The patient was assessed as FST I. A female subject aged approximately 35. A dermoscopic image of a skin lesion.
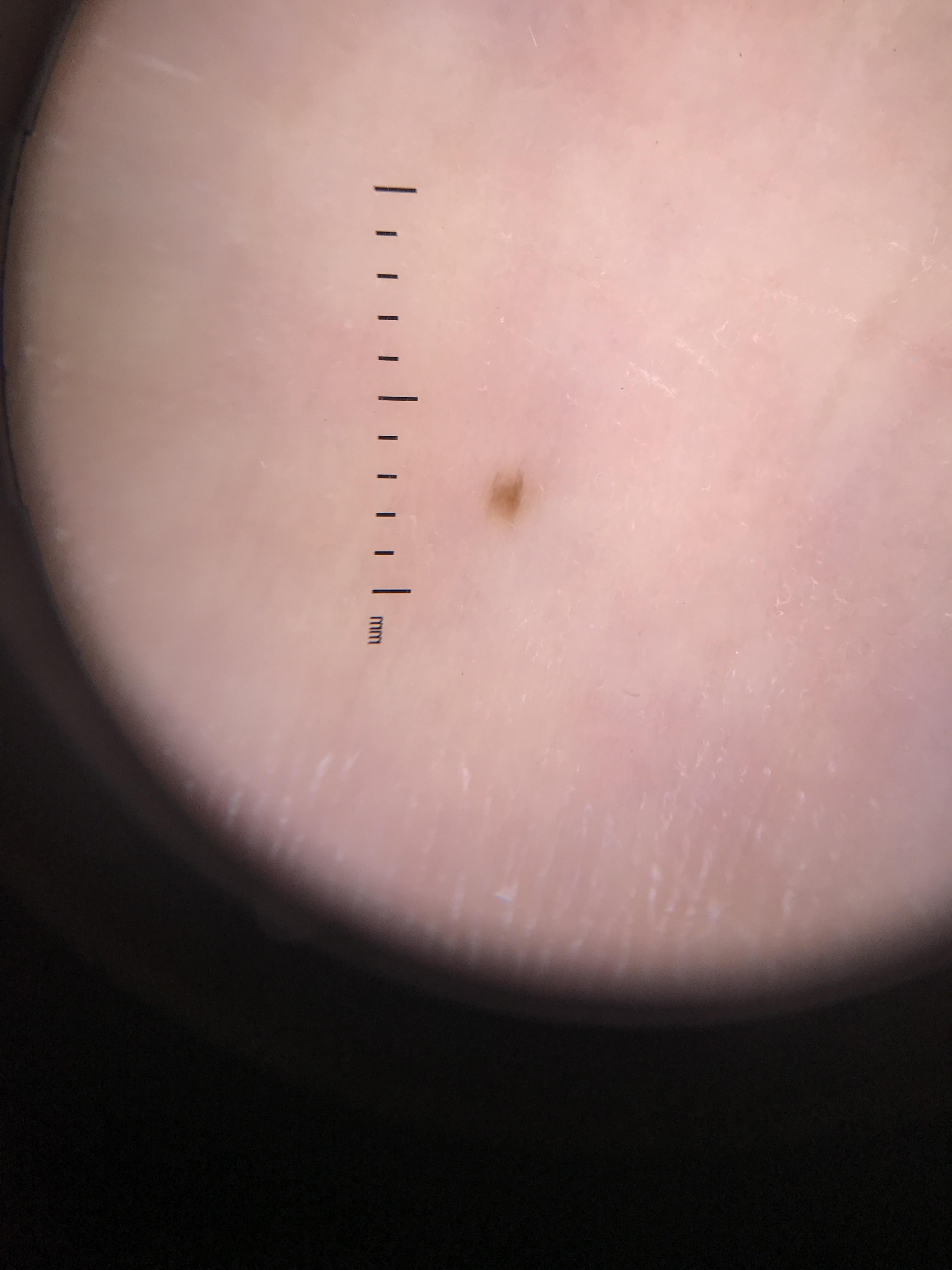body site: an acral site (palms or soles); diagnosis: Nevus (clinical impression).